A dermoscopy image of a single skin lesion.
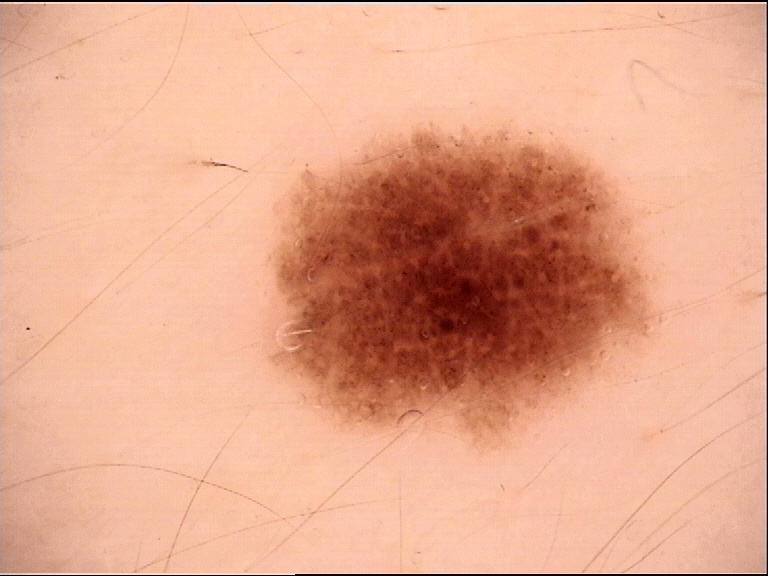This is a banal lesion.
The diagnosis was a junctional nevus.